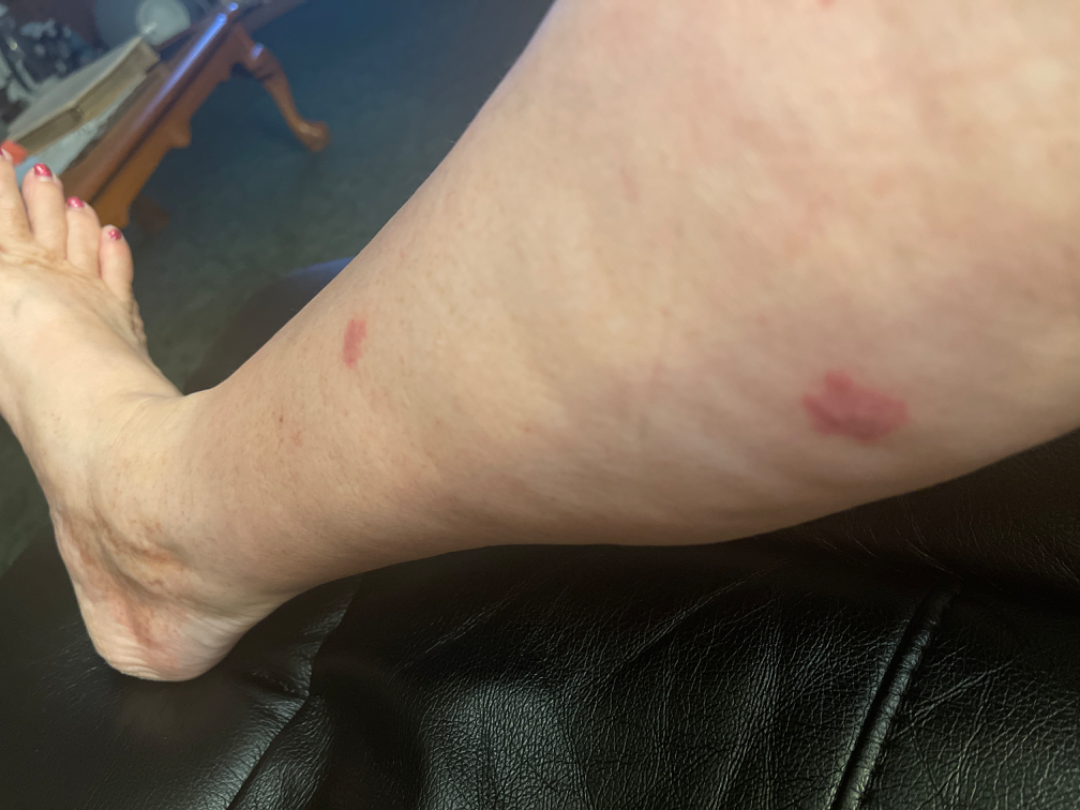History:
Fitzpatrick phototype I; human graders estimated MST 2–3. An image taken at a distance. No relevant systemic symptoms. Reported lesion symptoms include bothersome appearance, itching and darkening. Located on the leg.
Impression:
On remote dermatologist review: Hemangioma (0.54); Insect Bite (0.23); Tufted angioma of skin (0.23).